A male subject about 60 years old. Contact-polarized dermoscopy of a skin lesion.
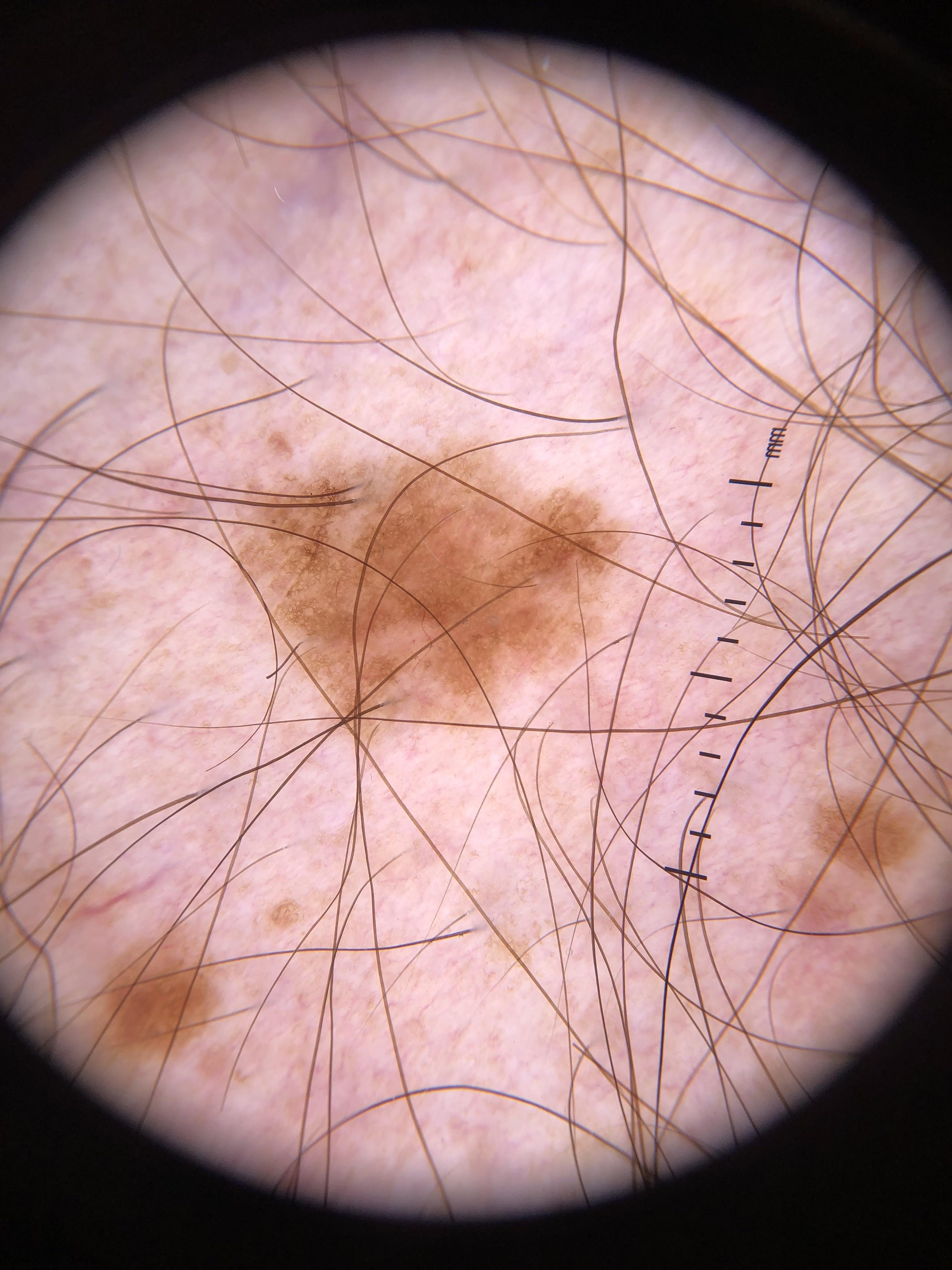The lesion is on a lower extremity. Confirmed on histopathology as a nevus.